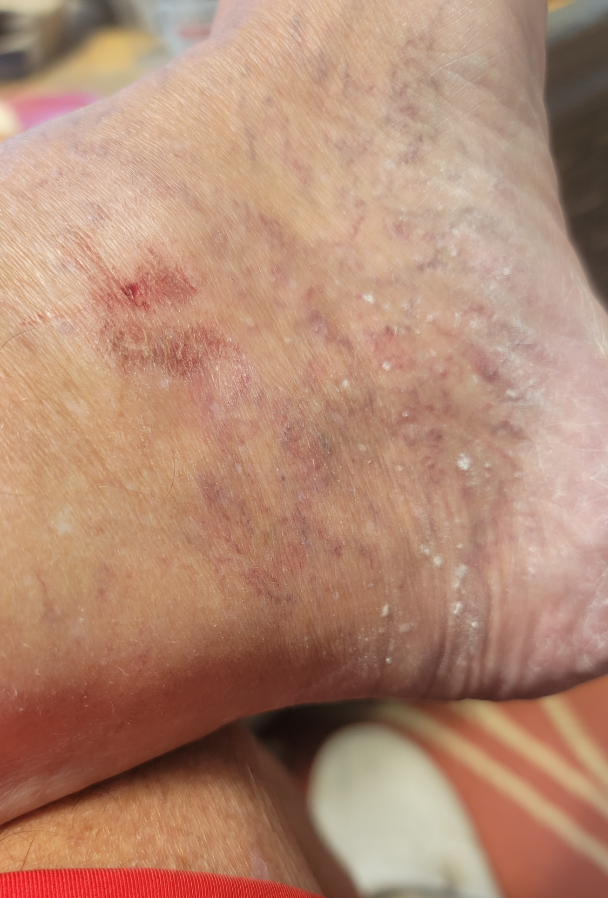The lesion is described as raised or bumpy and rough or flaky.
Skin tone: Fitzpatrick phototype IV; non-clinician graders estimated MST 5 (US pool) or 3 (India pool).
Self-categorized by the patient as a rash.
The lesion is associated with burning, bleeding, bothersome appearance and itching.
The contributor is a male aged 70–79.
This is a close-up image.
The top or side of the foot is involved.
The patient indicates the condition has been present for one to three months.
On teledermatology review: Stasis Dermatitis (possible); Tinea (possible); Eczema (possible).